The patient reports itching. The patient reports the lesion is fluid-filled. An image taken at a distance. Female patient, age 60–69. The patient reports the condition has been present for about one day:
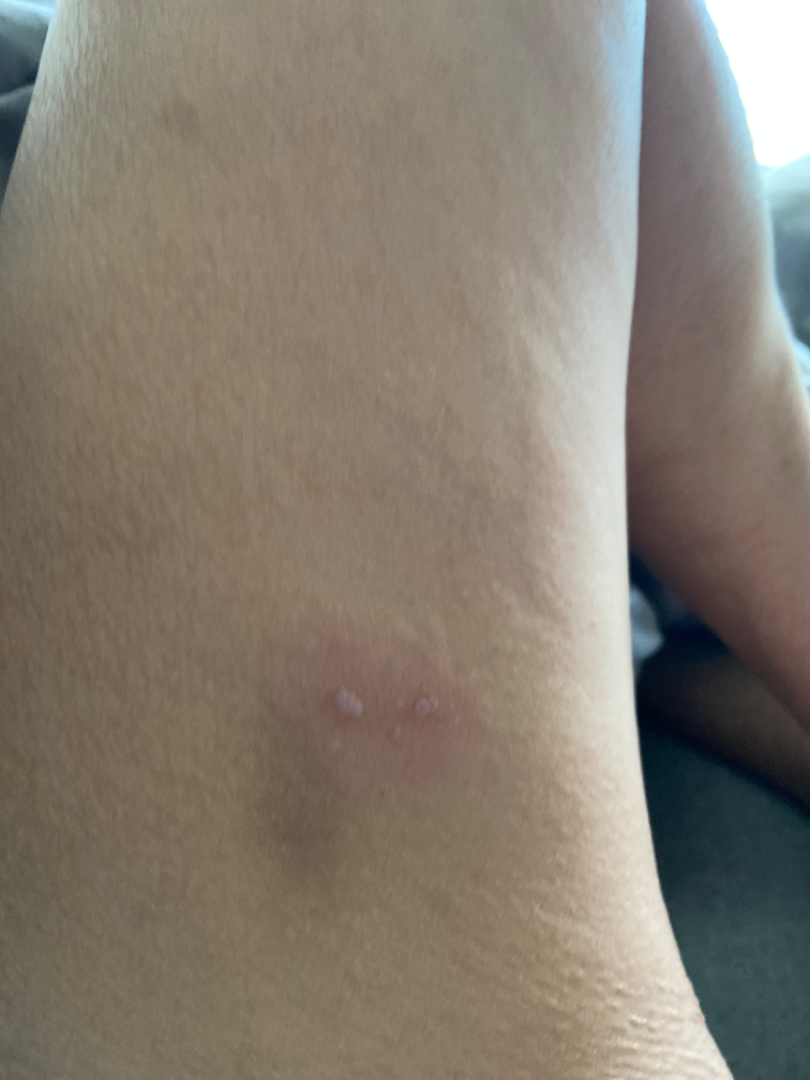Review:
On dermatologist assessment of the image: favoring Herpes Simplex; an alternative is Impetigo; also raised was Herpes Zoster.